A dermoscopic view of a skin lesion. A female patient aged approximately 80:
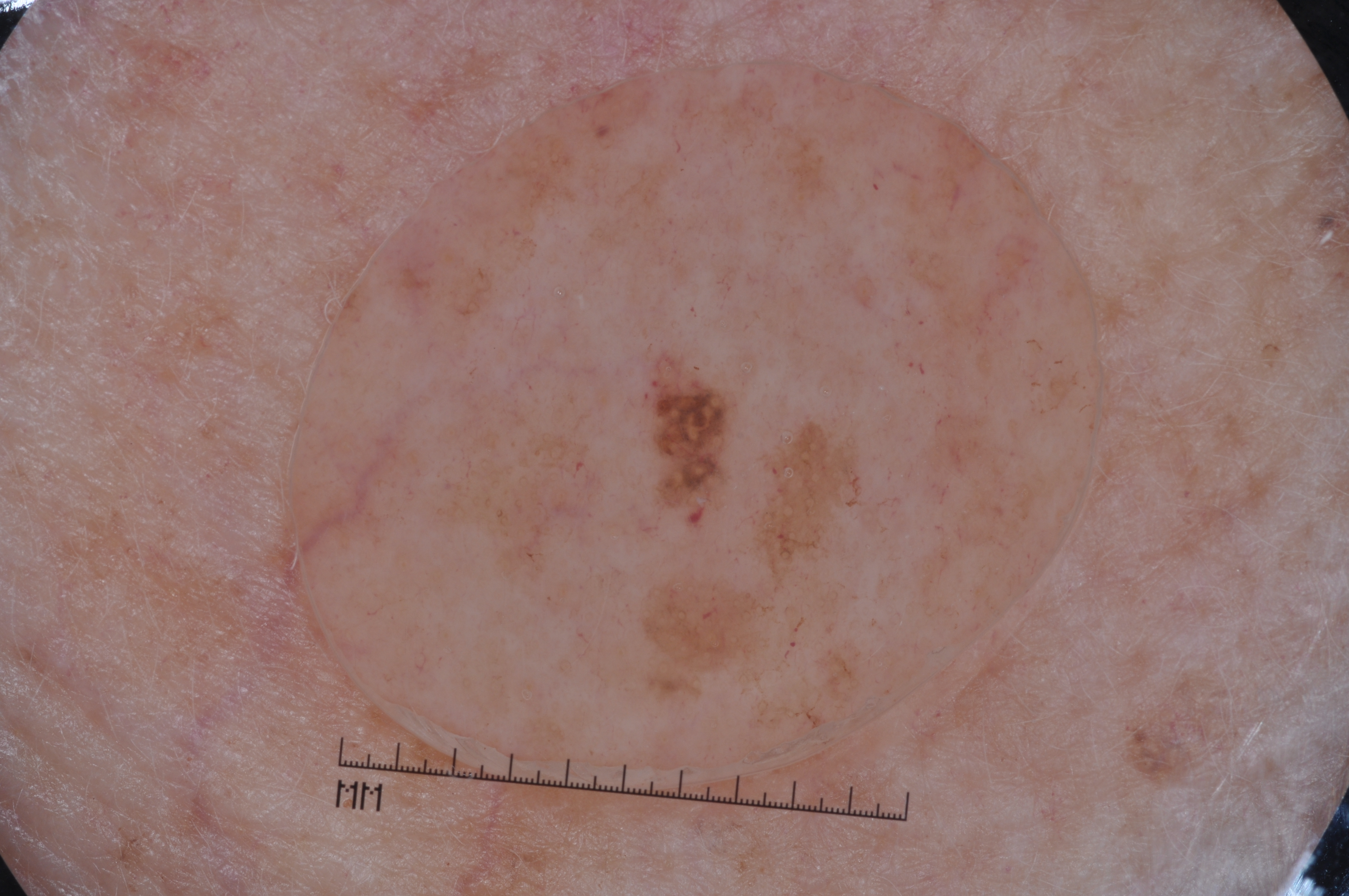location = 649 386 736 518; dermoscopic features assessed but absent = milia-like cysts, negative network, streaks, and pigment network; impression = a melanoma.